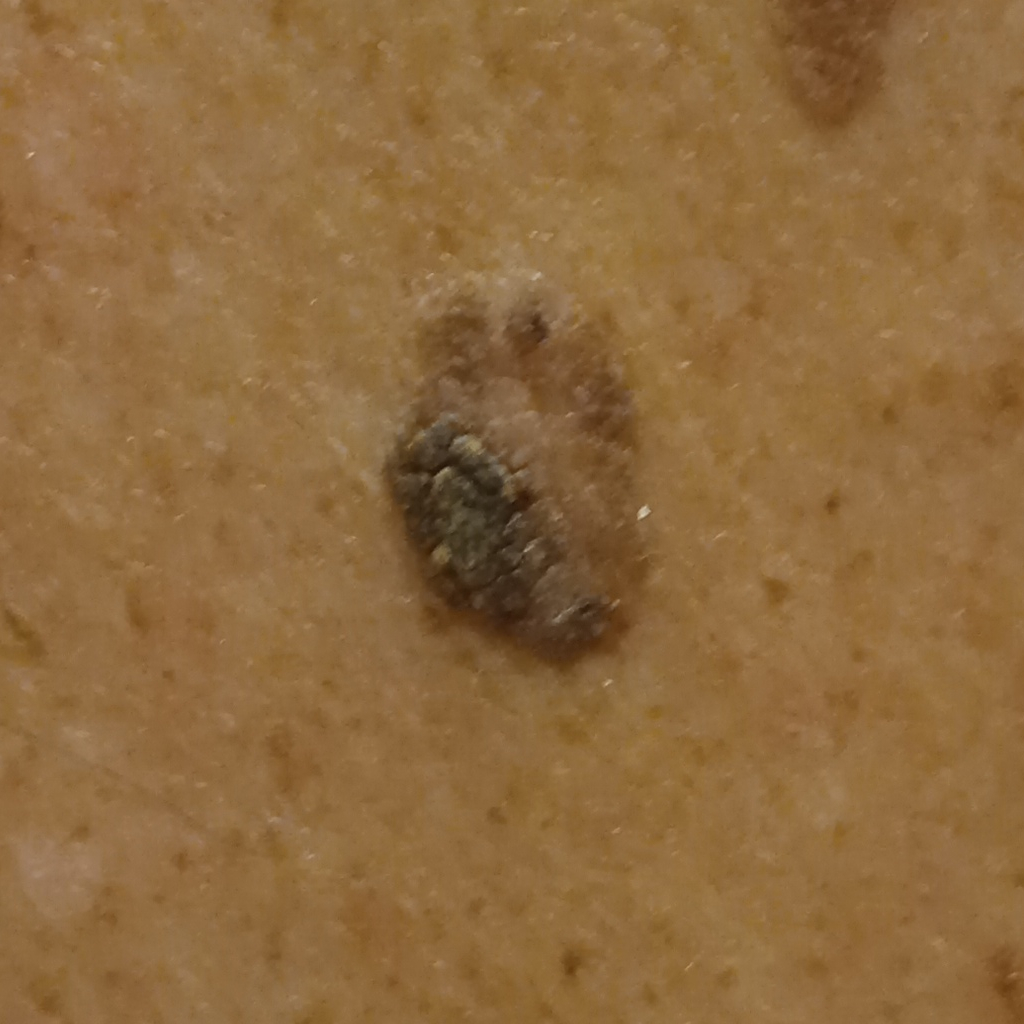diagnostic label = seborrheic keratosis (dermatologist consensus).